Located on the back of the hand. This image was taken at an angle. The patient is 18–29, female.
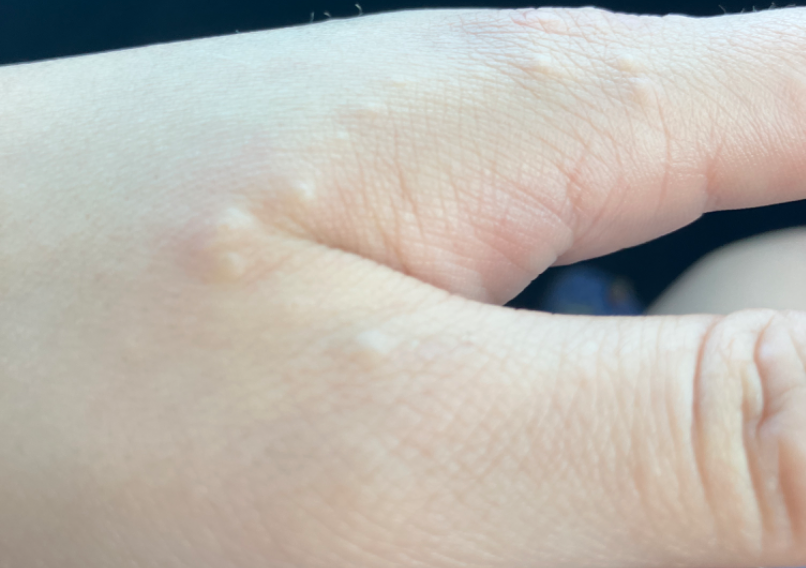{
  "assessment": "indeterminate from the photograph"
}